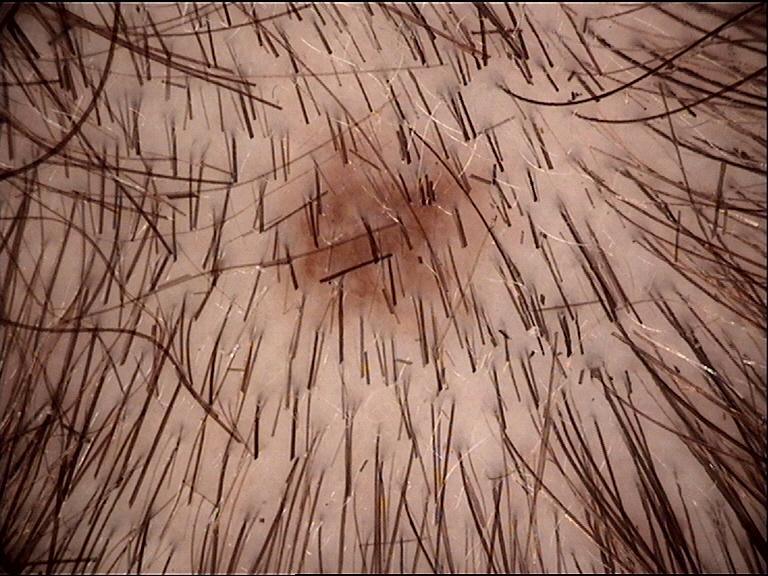Classified as a dysplastic junctional nevus.